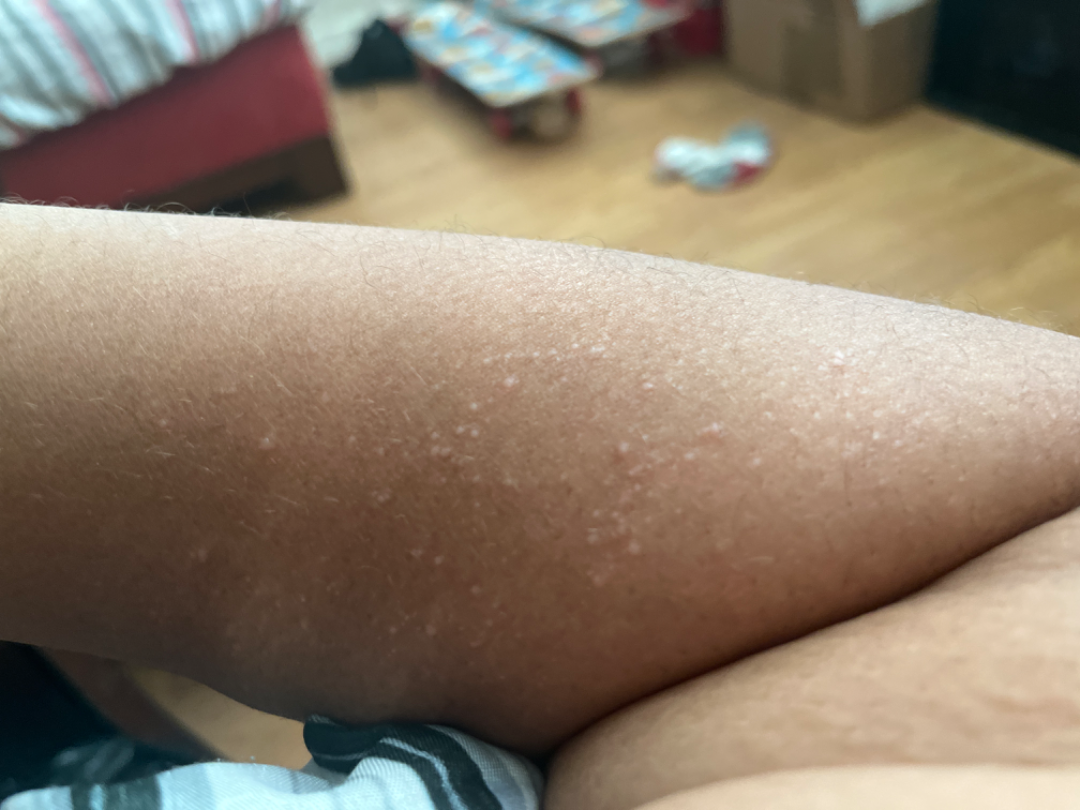An image taken at an angle.
Present for one to four weeks.
The arm is involved.
The patient considered this a rash.
The patient is 30–39, female.
The reviewing dermatologists' impression was: the favored diagnosis is Eczema; also raised was Lichen nitidus; less likely is Keratosis pilaris.